The photo was captured at an angle. The affected area is the arm, front of the torso, head or neck and back of the hand:
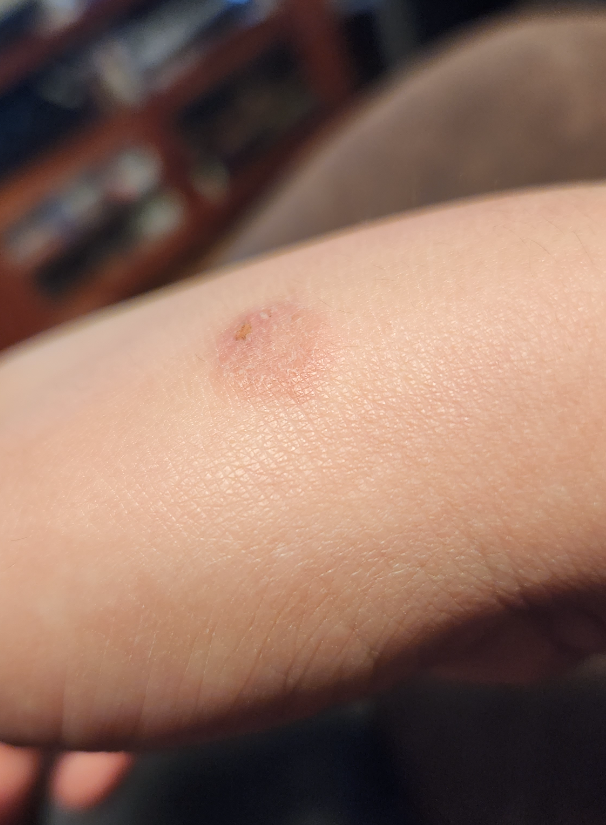Assessment: Most consistent with Eczema.